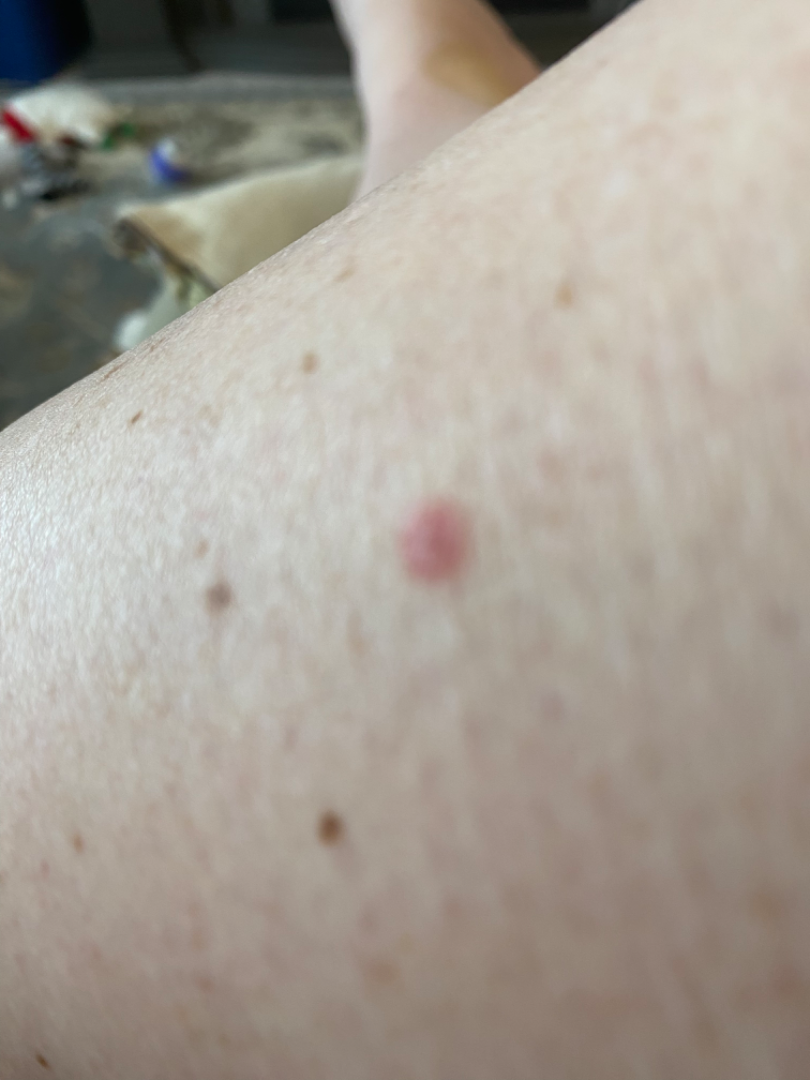assessment = indeterminate from the photograph.